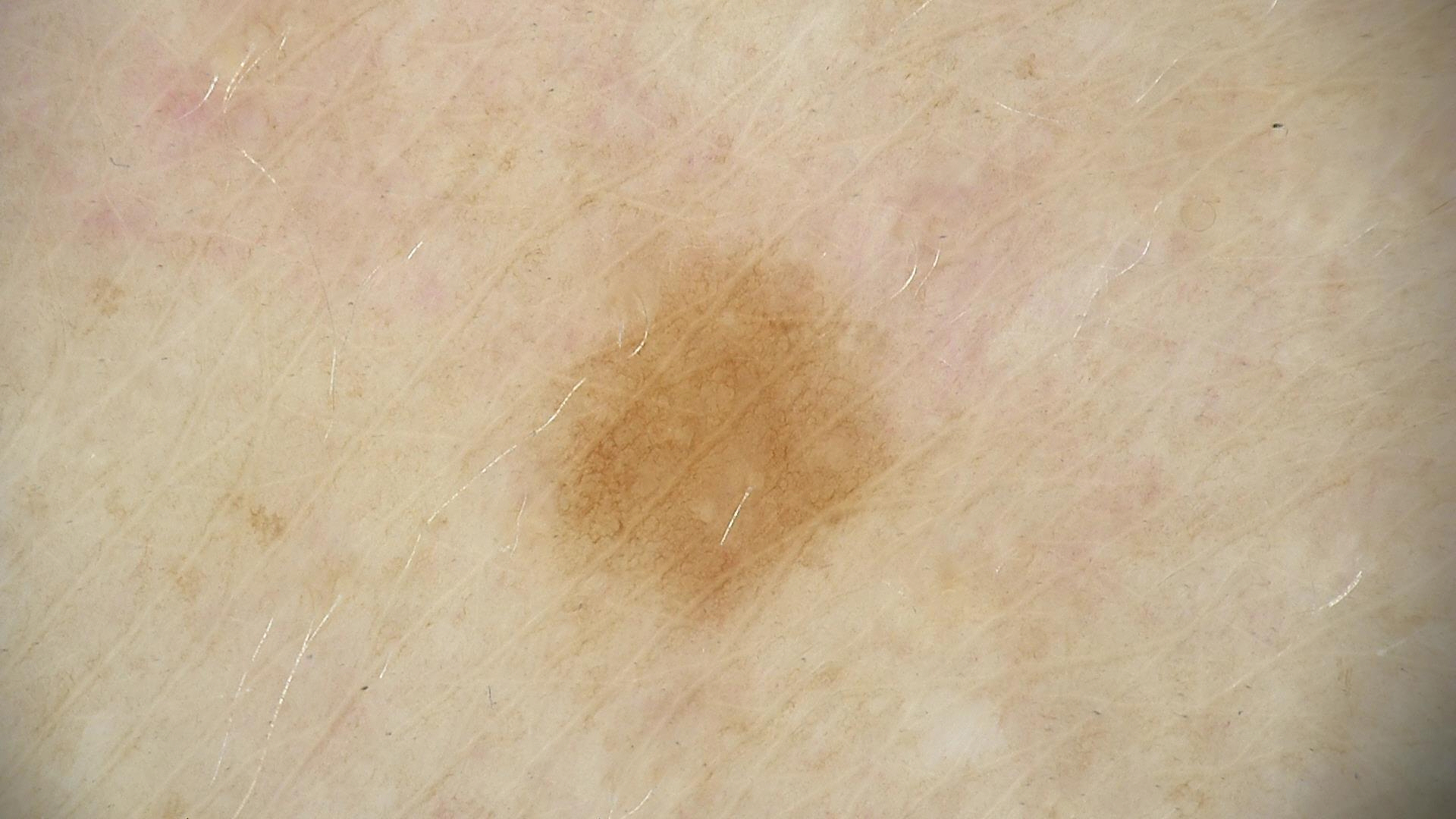Findings: Dermoscopy of a skin lesion. Impression: Diagnosed as a lentigo simplex.